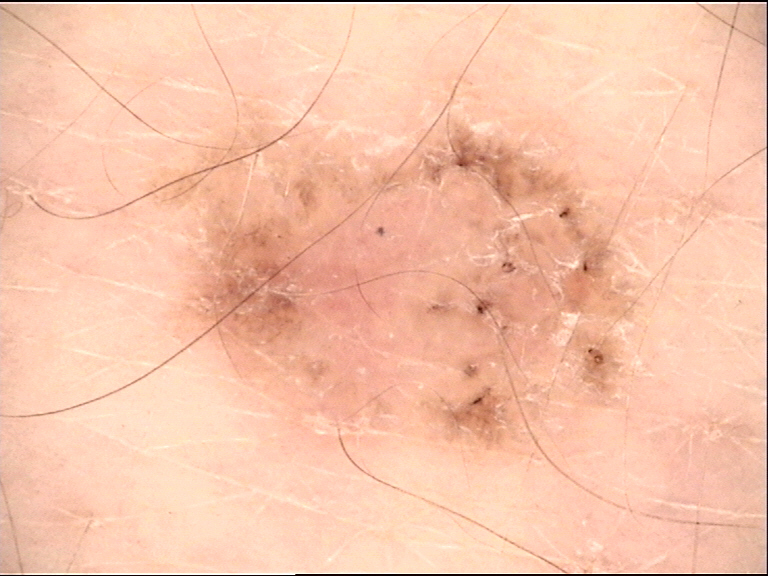Q: What kind of image is this?
A: dermoscopy
Q: What is the lesion category?
A: keratinocytic
Q: What is this lesion?
A: basal cell carcinoma (biopsy-proven)